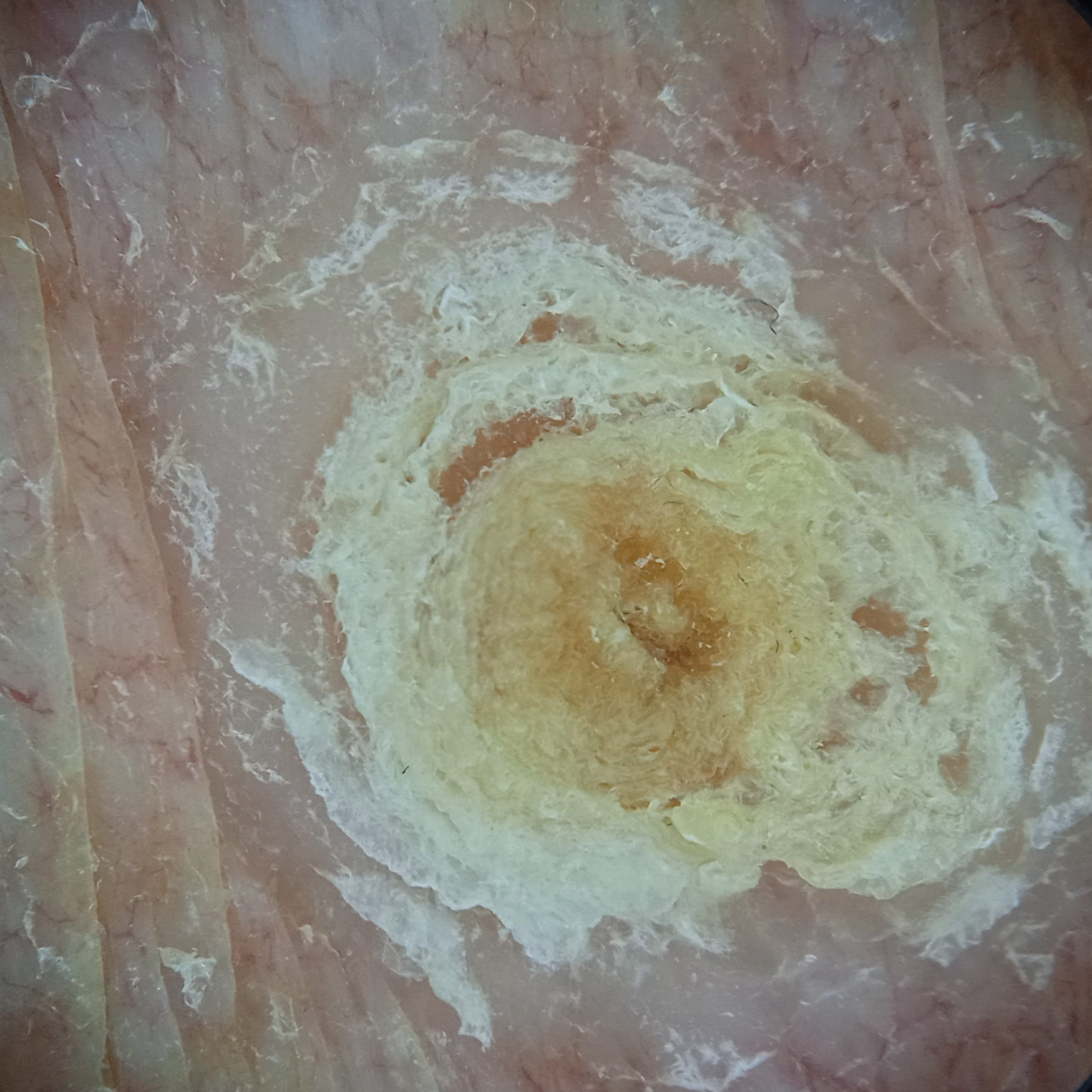{
  "image": "dermoscopic image",
  "risk_factors": {
    "positive": [
      "a personal history of cancer",
      "a family history of skin cancer"
    ]
  },
  "sun_reaction": "skin tans without first burning",
  "referral": "research study (no referral diagnosis)",
  "lesion_size": {
    "diameter_mm": 12.5
  },
  "diagnosis": {
    "name": "squamous cell carcinoma",
    "malignancy": "malignant"
  }
}